Acquired for a research image collection, with no referral diagnosis · a dermoscopy image of a skin lesion: 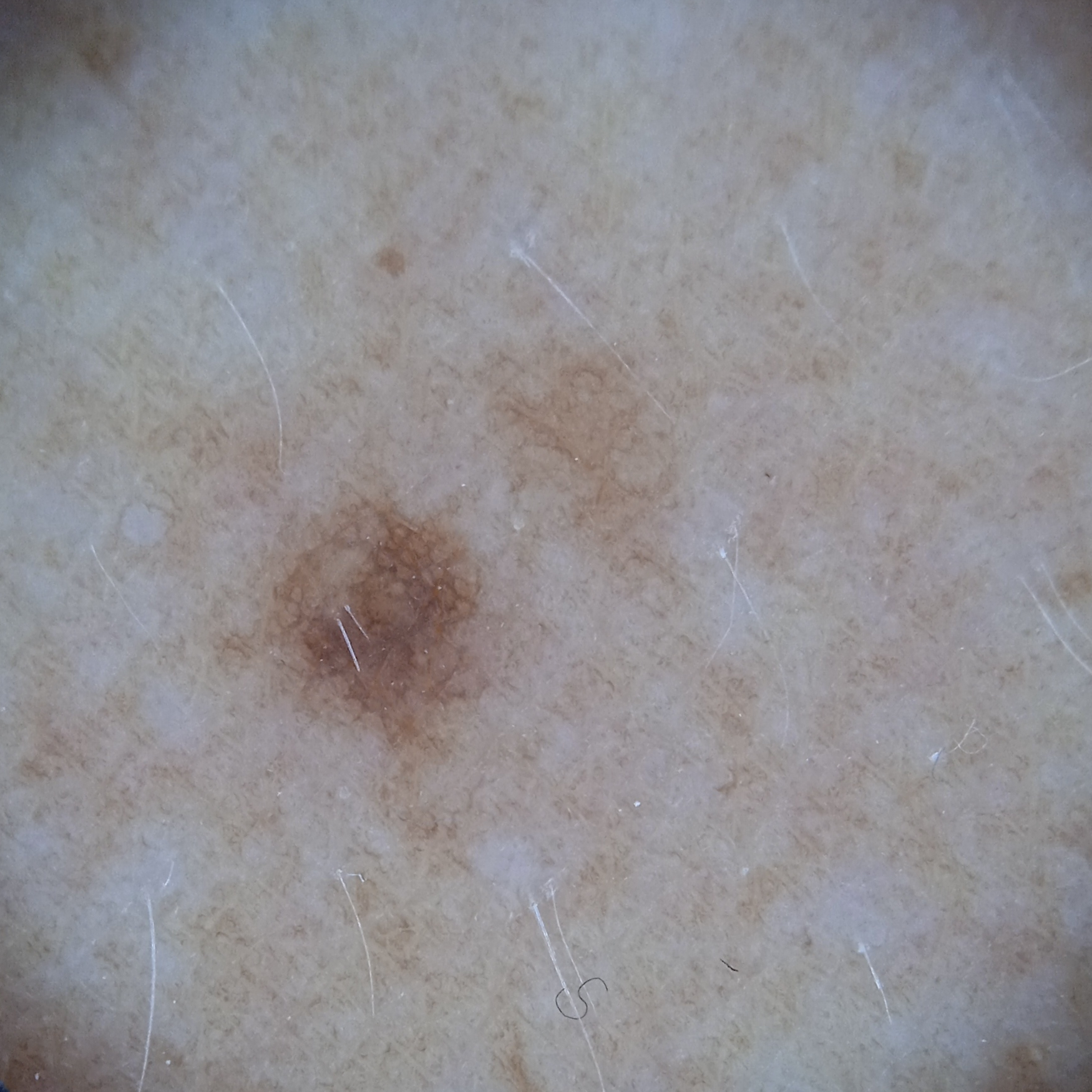Summary: Located on an arm. Conclusion: The consensus diagnosis for this lesion was a melanocytic nevus.